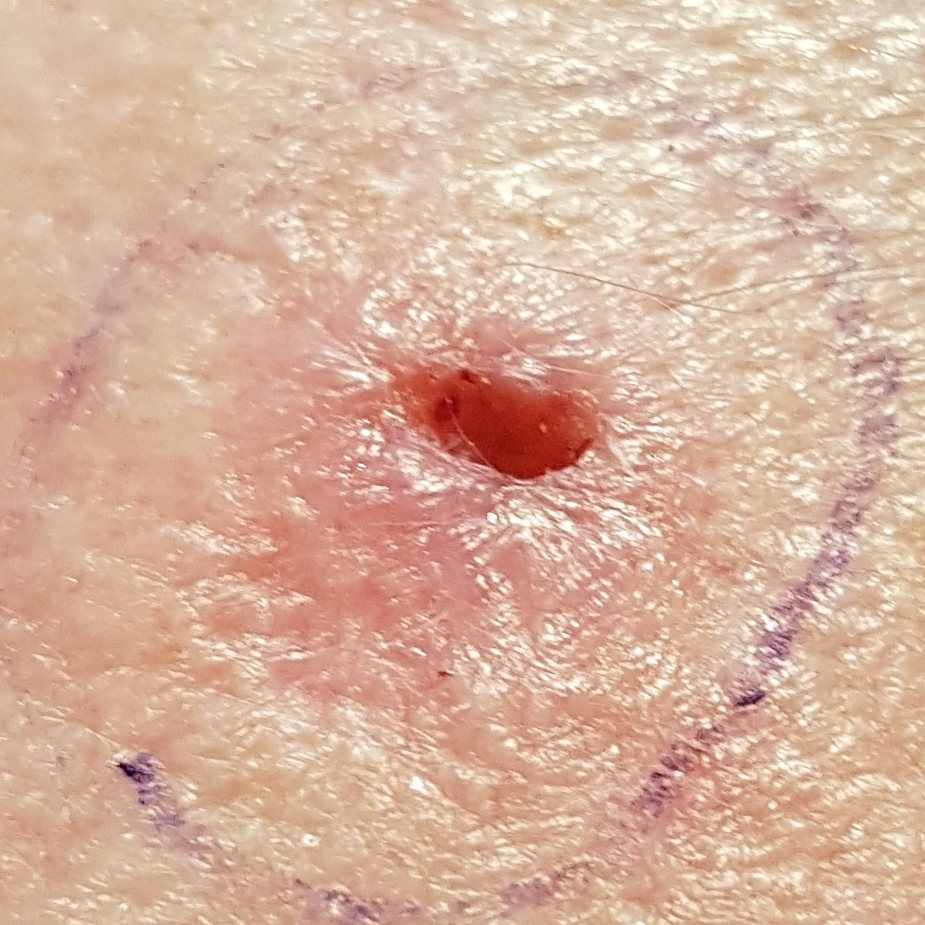A clinical photograph of a skin lesion.
A male patient 58 years of age.
Fitzpatrick skin type I.
The lesion measures approximately 10 × 7 mm.
Confirmed on histopathology as a malignancy — a basal cell carcinoma.